The affected area is the arm, the patient is a male aged 18–29, a close-up photograph.
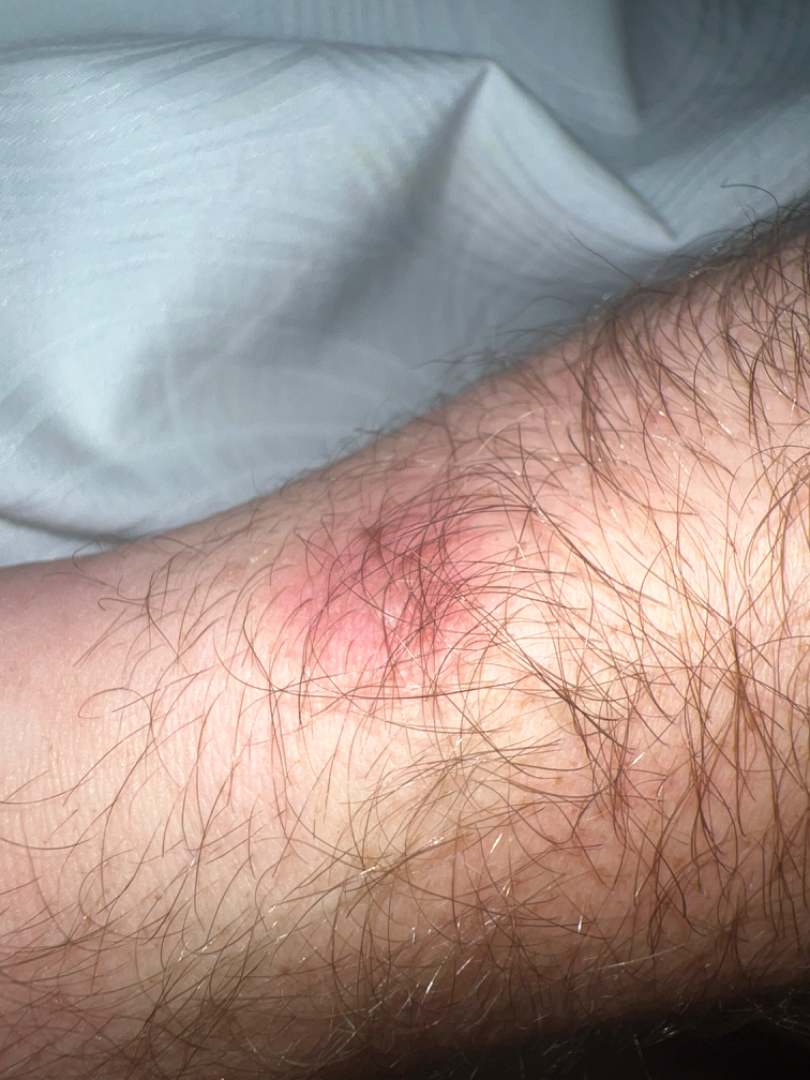The reviewing dermatologist was unable to assign a differential diagnosis from the image.